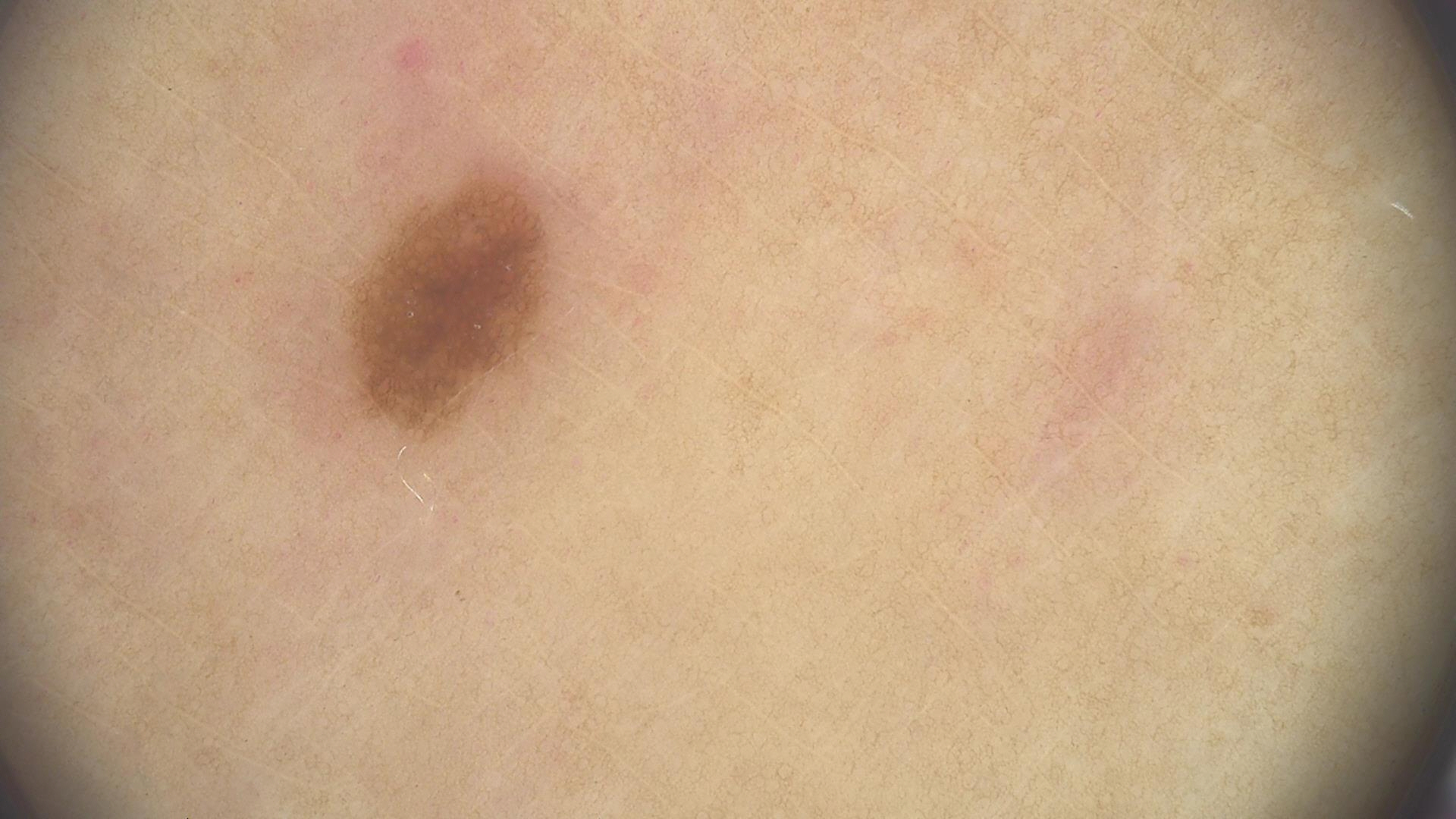- image type · dermatoscopy
- assessment · junctional nevus (expert consensus)